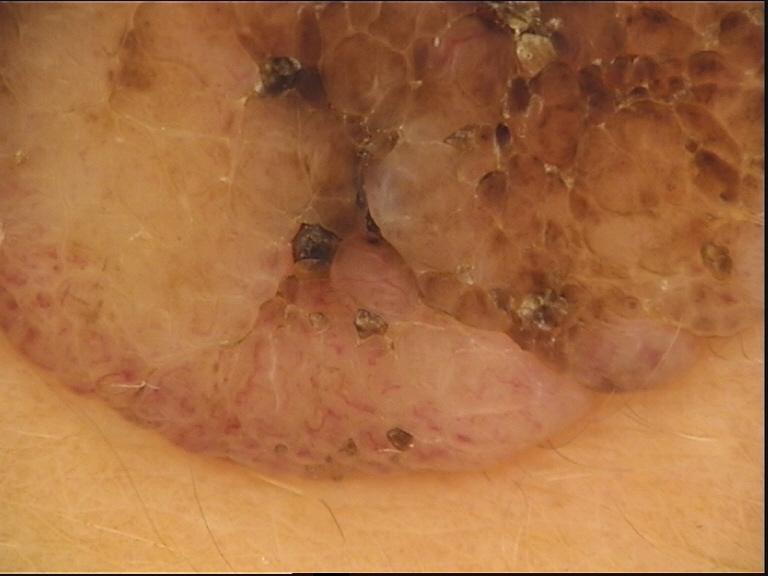Consistent with a dermal nevus.